A dermoscopic close-up of a skin lesion.
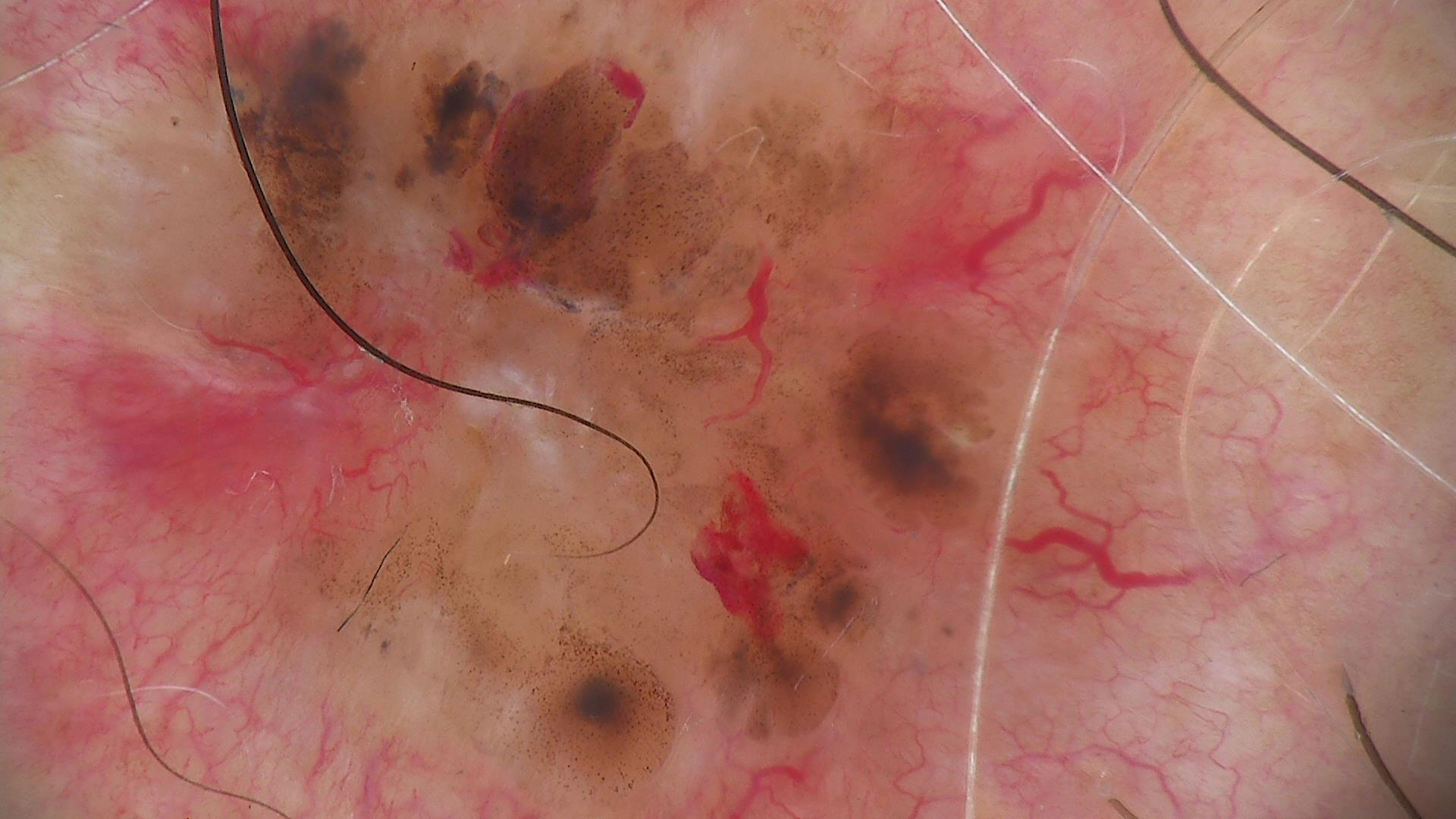diagnosis = basal cell carcinoma (biopsy-proven)